The affected area is the top or side of the foot. This image was taken at an angle.
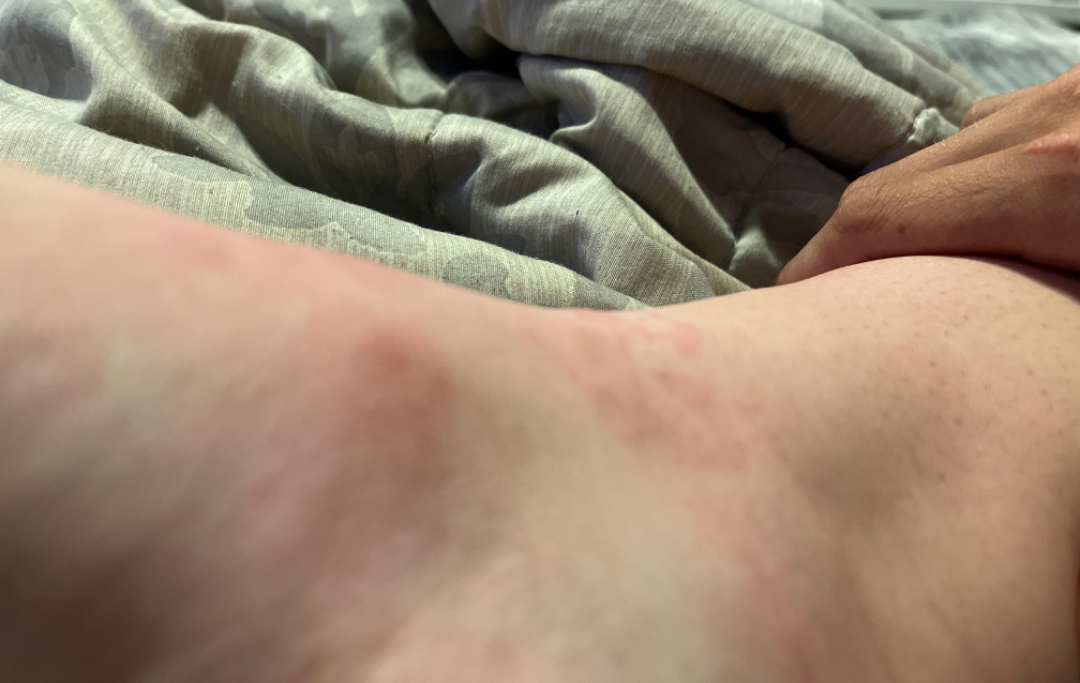The image was not sufficient for the reviewer to characterize the skin condition. Symptoms reported: burning, itching and bothersome appearance. Texture is reported as raised or bumpy. The contributor notes the condition has been present for less than one week.